Self-categorized by the patient as skin that appeared healthy to them, the leg is involved, the patient also reports fatigue, this is a close-up image, the condition has been present for one to four weeks, reported lesion symptoms include bothersome appearance.
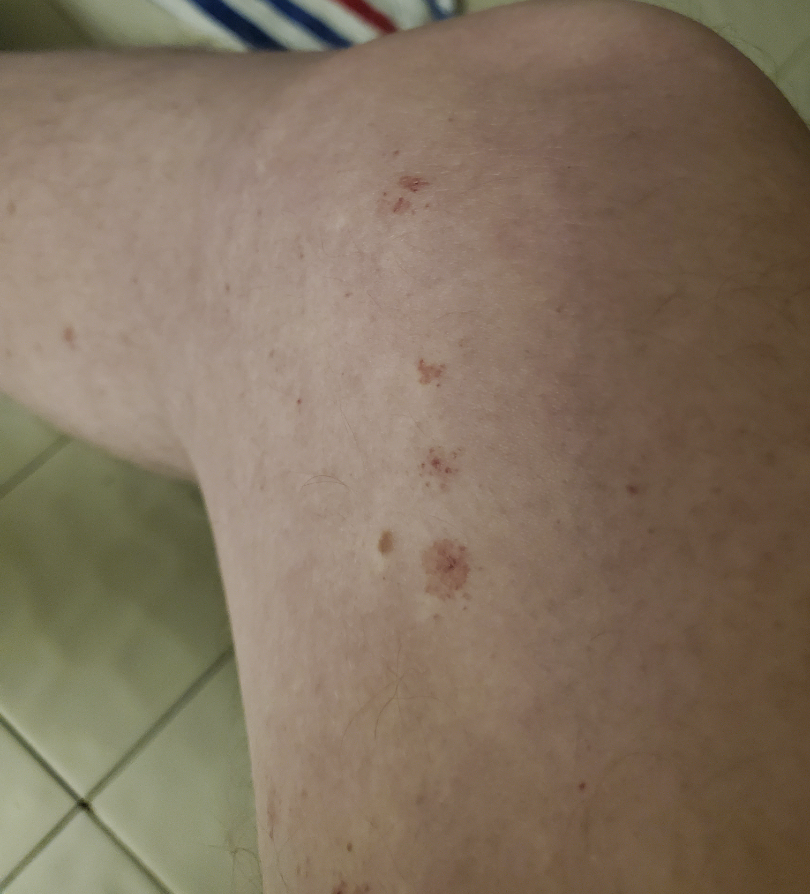– assessment: not assessable